The subject is a male aged 53 to 57. Dermoscopy of a skin lesion — 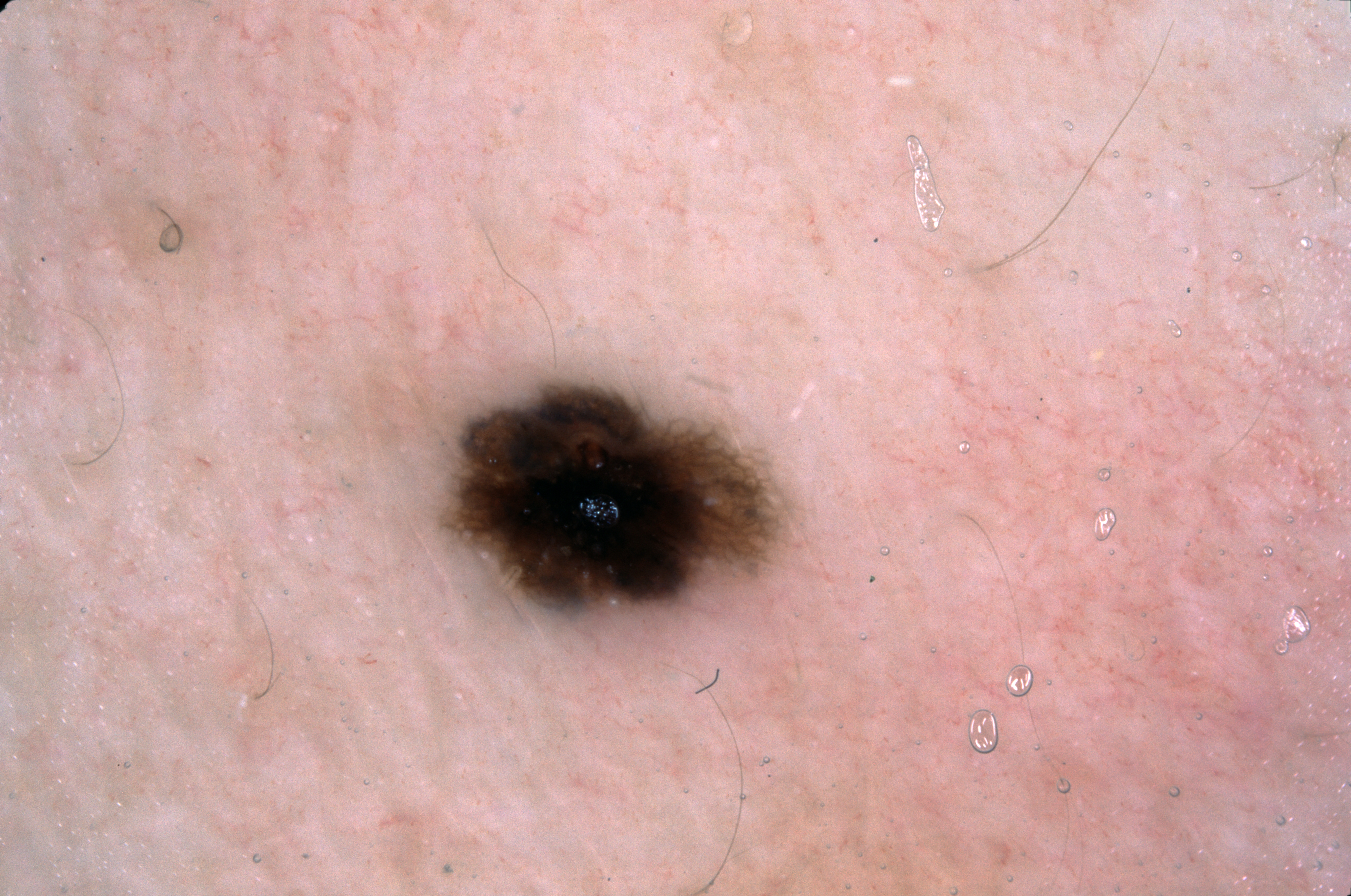The lesion occupies roughly 5% of the field. Dermoscopic assessment notes milia-like cysts and pigment network; no negative network or streaks. As (left, top, right, bottom), lesion location: box(444, 378, 791, 623). Consistent with a melanocytic nevus.